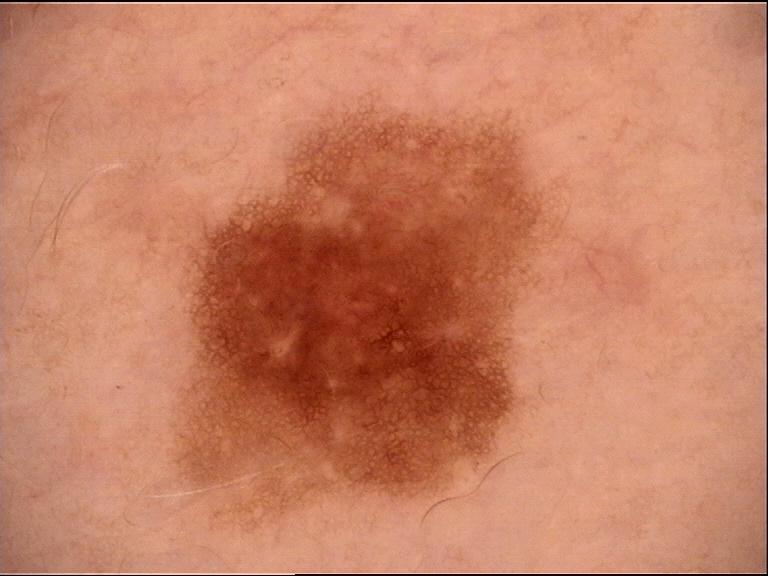A dermoscopy image of a single skin lesion. The diagnostic label was a benign lesion — a dysplastic junctional nevus.